Close-up view. The leg is involved. The contributor is 70–79, male:
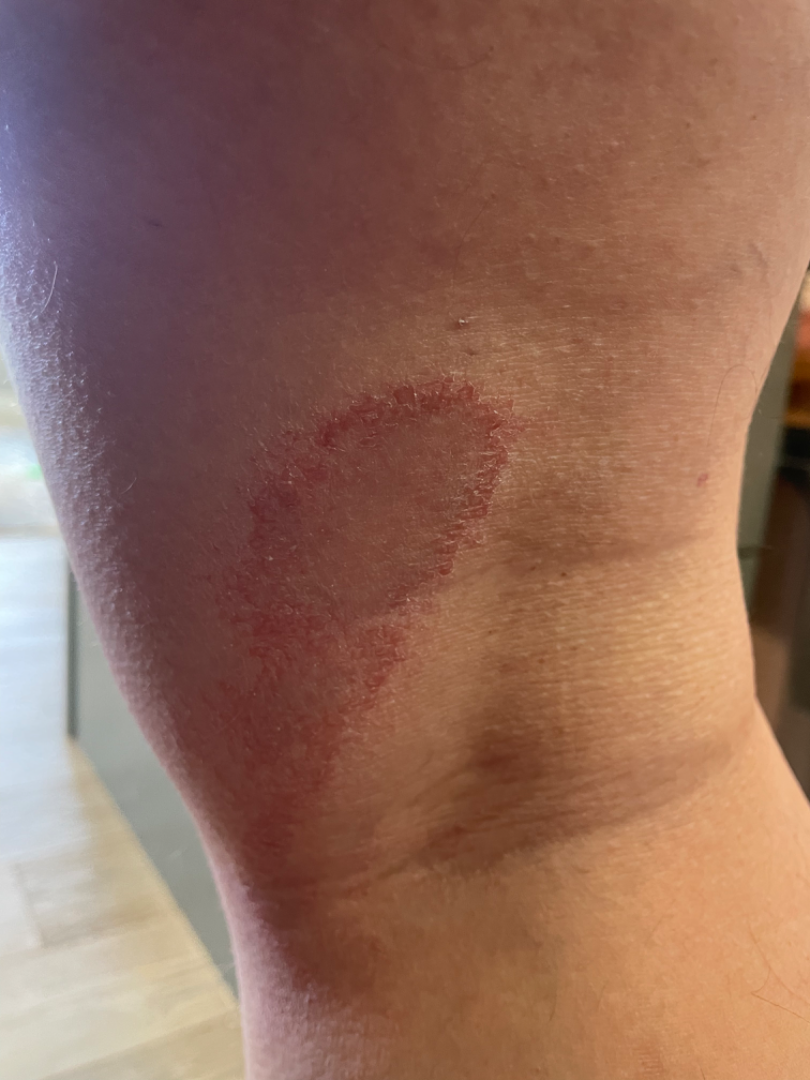Skin tone: Fitzpatrick skin type III; human graders estimated MST 3 or 5.
The lesion is described as rough or flaky.
The patient described the issue as a rash.
No relevant lesion symptoms reported.
On teledermatology review: favoring Tinea.